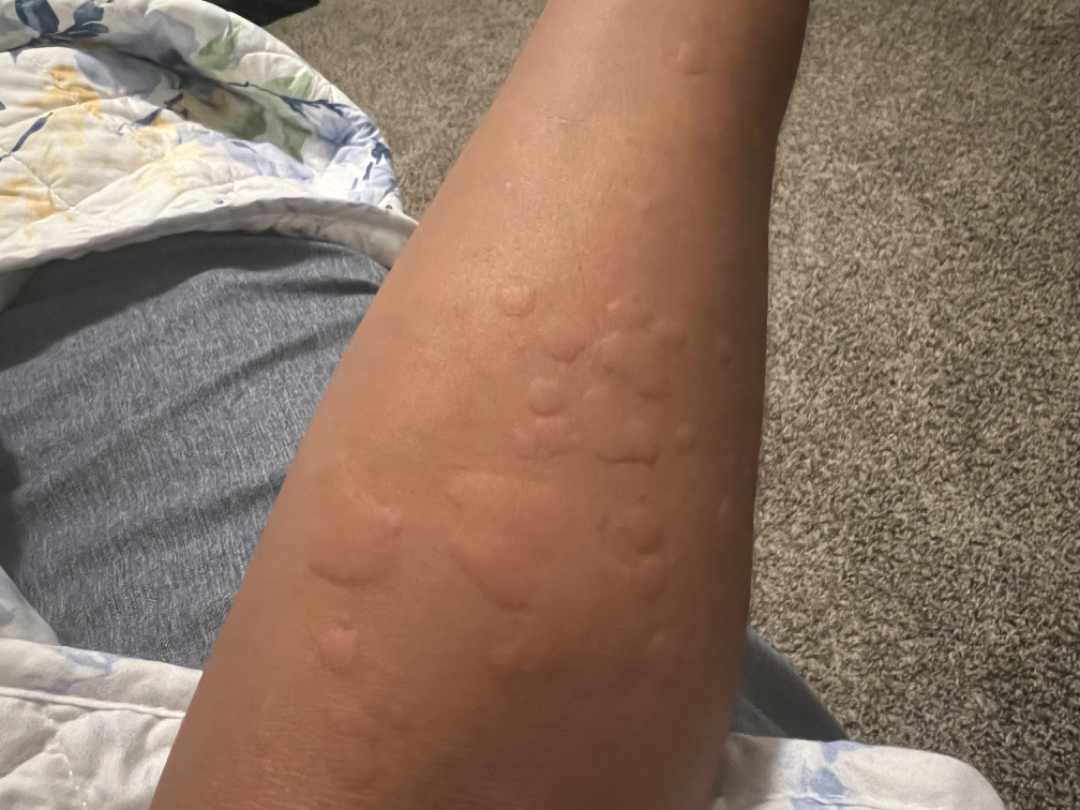Findings: A single dermatologist reviewed the case: favoring Urticaria; also on the differential is Insect Bite; also raised was Allergic Contact Dermatitis.